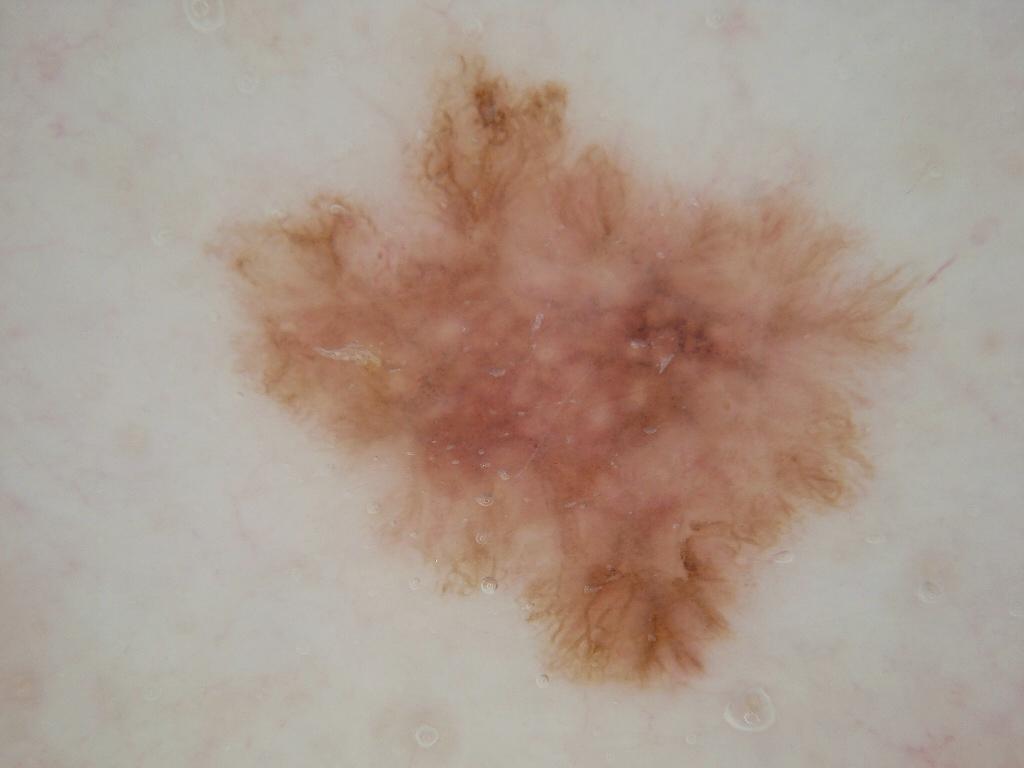The subject is a male in their 60s. This is a dermoscopic photograph of a skin lesion. The lesion is located at left=201, top=30, right=928, bottom=700. Dermoscopic examination shows pigment network and streaks. The lesion occupies roughly 35% of the field. Clinically diagnosed as a melanocytic nevus.